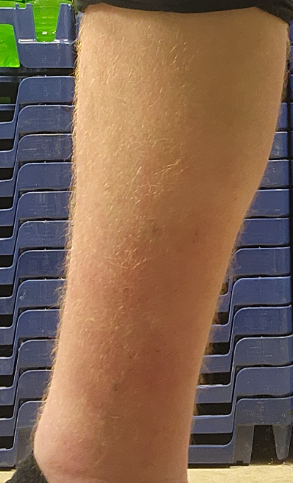associated systemic symptoms: none reported | framing: at a distance | anatomic site: front of the torso, leg, back of the hand and arm | surface texture: raised or bumpy | lesion symptoms: bothersome appearance, burning, bleeding, enlargement and itching | contributor: male, age 30–39 | history: one to four weeks | assessment: the differential includes Contact dermatitis and Stasis Dermatitis, with no clear leading consideration.